The photo was captured at an angle. Texture is reported as raised or bumpy. The patient described the issue as a rash. The lesion involves the front of the torso. Skin tone: Fitzpatrick phototype I; lay reviewers estimated Monk Skin Tone 2 or 3 — 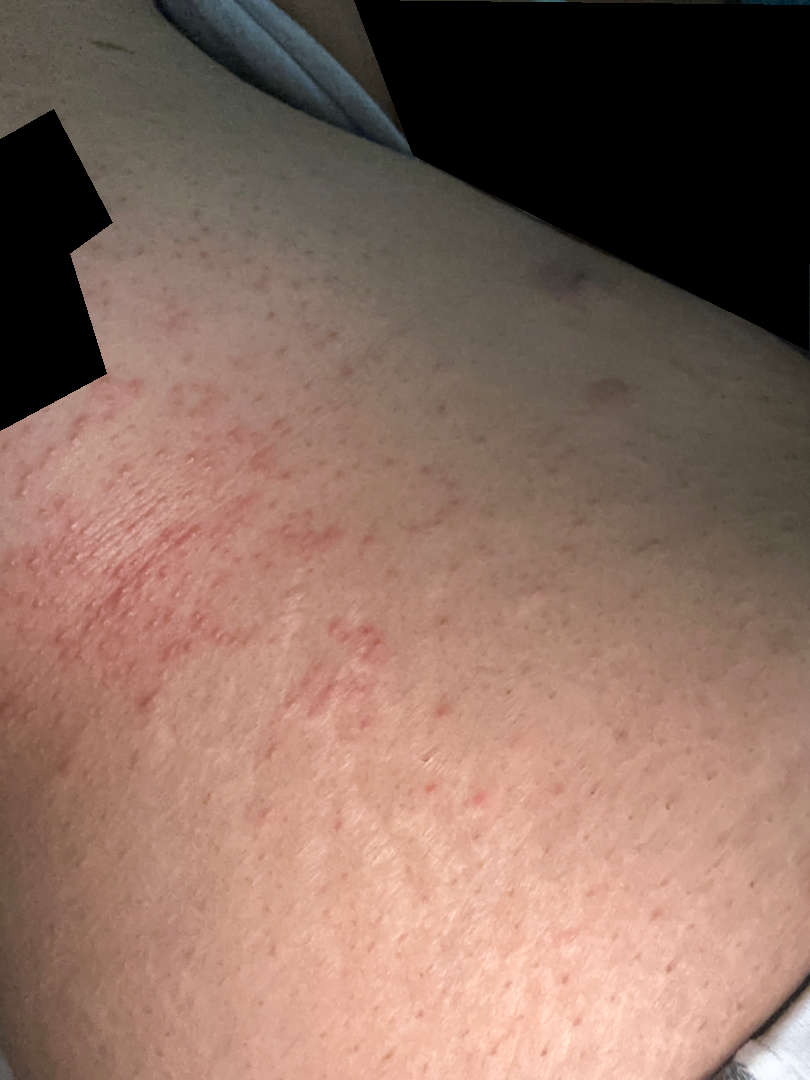Findings: Three dermatologists each reviewed the case: favoring Hypersensitivity; also on the differential is Drug Rash; also consider Viral Exanthem; less likely is Allergic Contact Dermatitis.